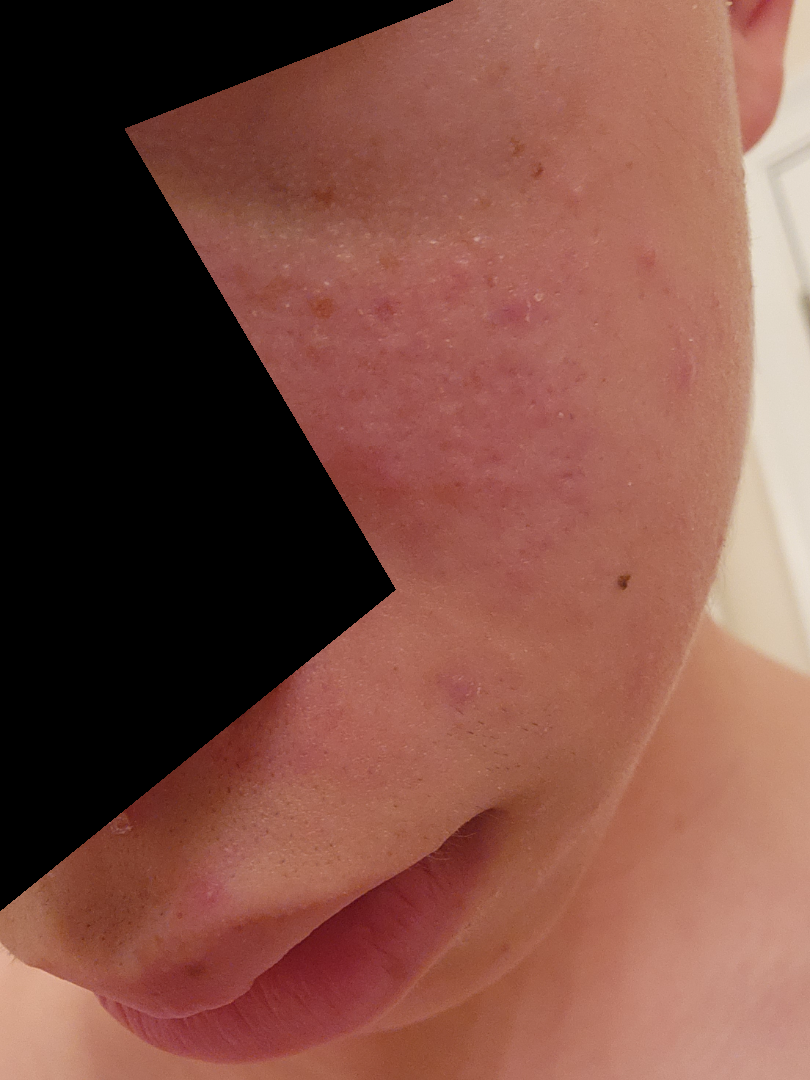Skin tone: Fitzpatrick skin type I; non-clinician graders estimated 2 on the MST. Texture is reported as raised or bumpy. Close-up view. Self-categorized by the patient as acne. The lesion involves the head or neck. On dermatologist assessment of the image: favoring Acne; also consider Perioral Dermatitis.